Dermoscopy of a skin lesion; a male subject, aged around 15.
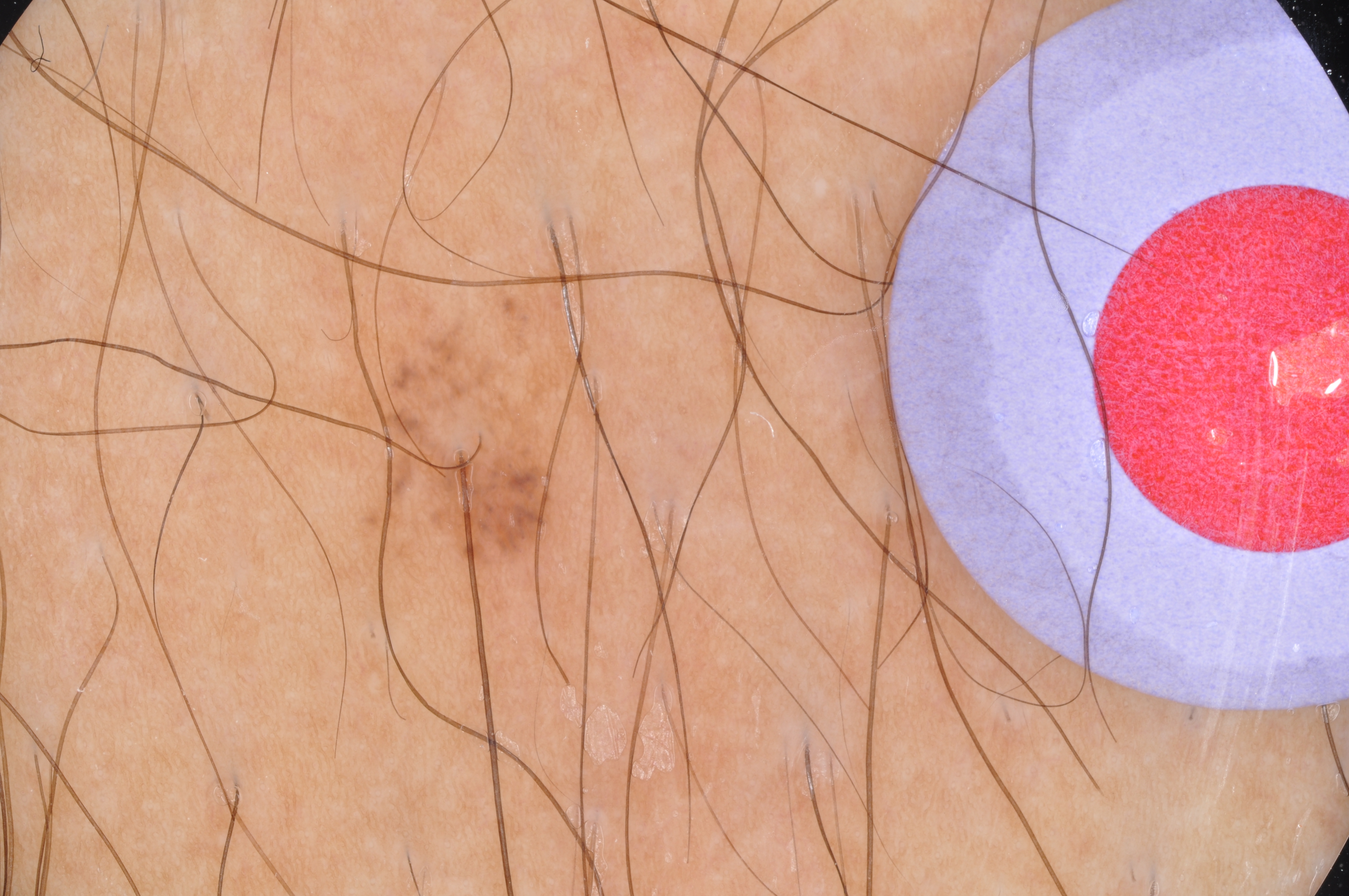Case summary:
* dermoscopic findings — globules
* lesion bbox — x1=350 y1=284 x2=582 y2=569
* extent — small
* diagnostic label — a melanocytic nevus, a benign skin lesion